Dermoscopy of a skin lesion, a male subject:
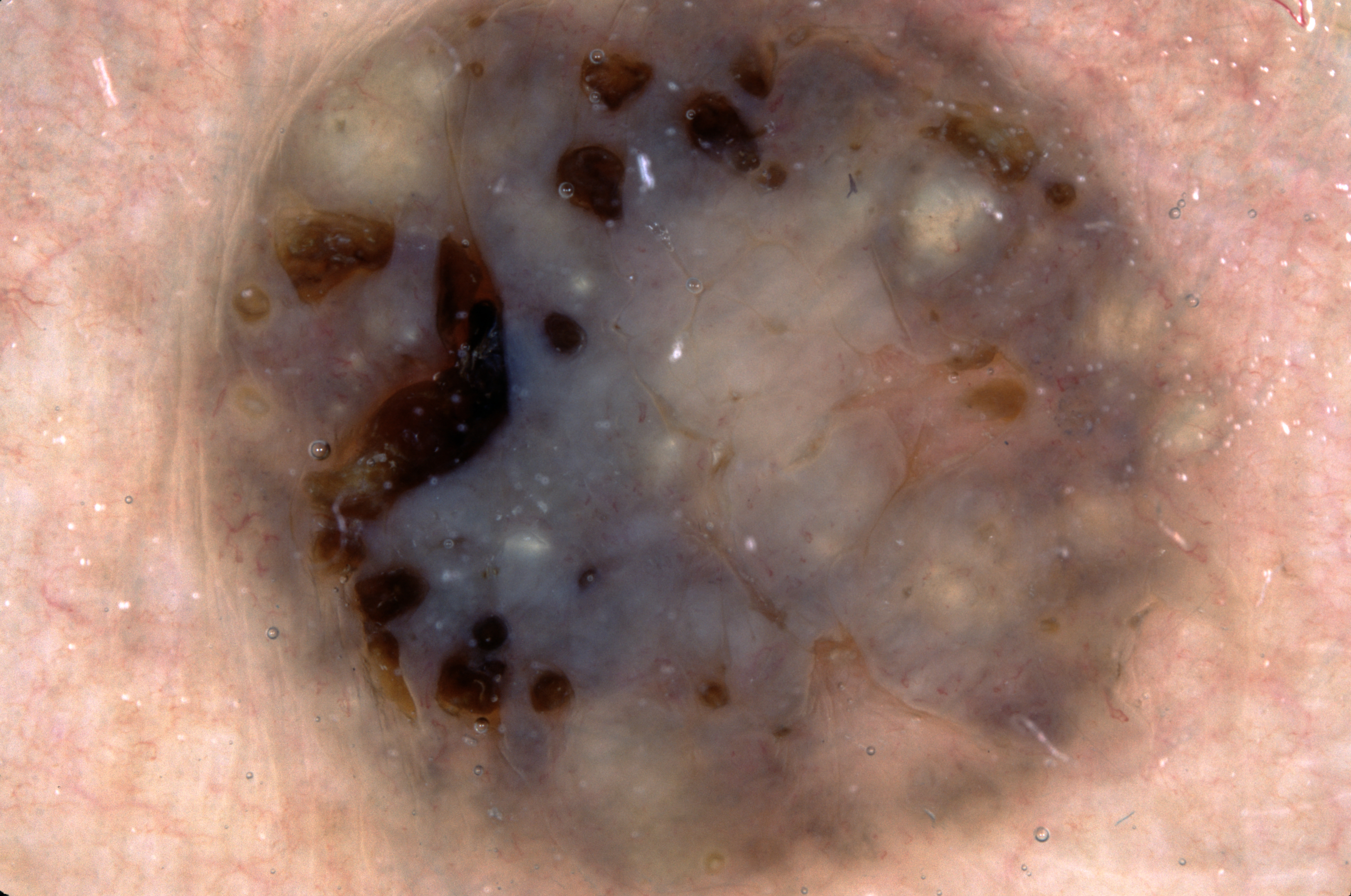The lesion is located at <box>158, 0, 1245, 895</box>.
Dermoscopy demonstrates milia-like cysts.
The lesion takes up a large portion of the image.
The diagnostic assessment was a seborrheic keratosis, a keratinocytic lesion.